The lesion is associated with itching · skin tone: Fitzpatrick phototype IV; lay reviewers estimated 5 on the Monk Skin Tone · a close-up photograph · the patient notes the lesion is raised or bumpy · the patient notes the condition has been present for about one day: 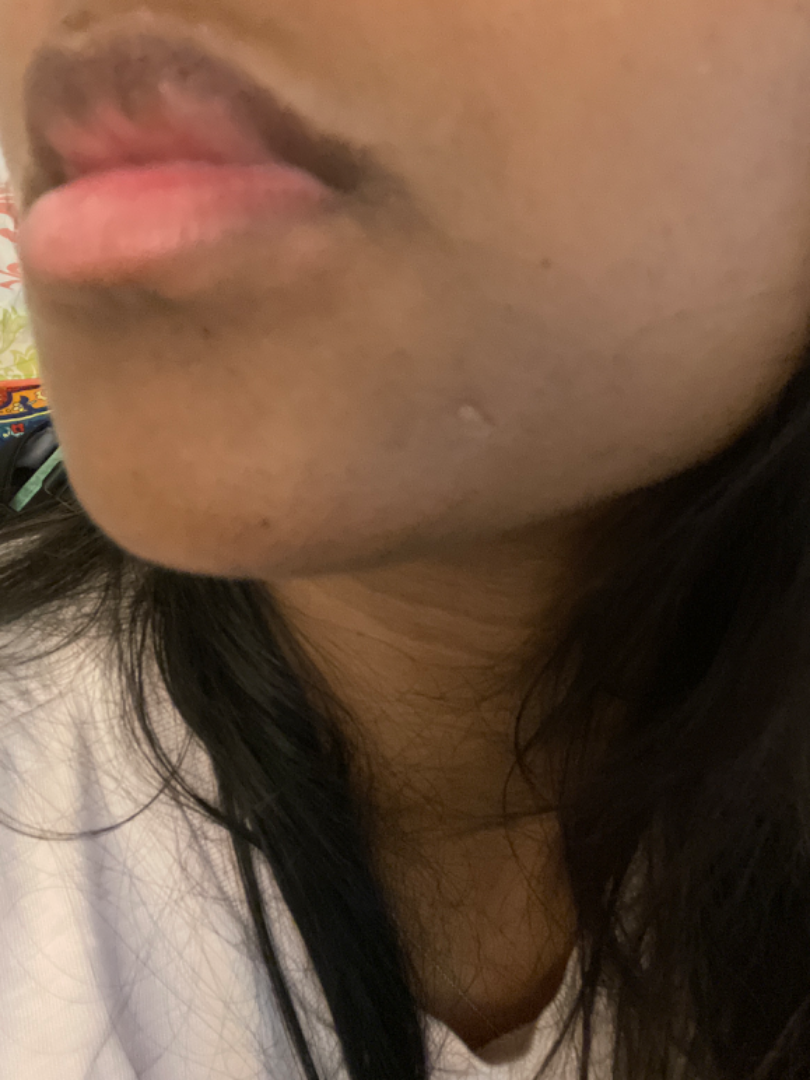Q: Could the case be diagnosed?
A: unable to determine